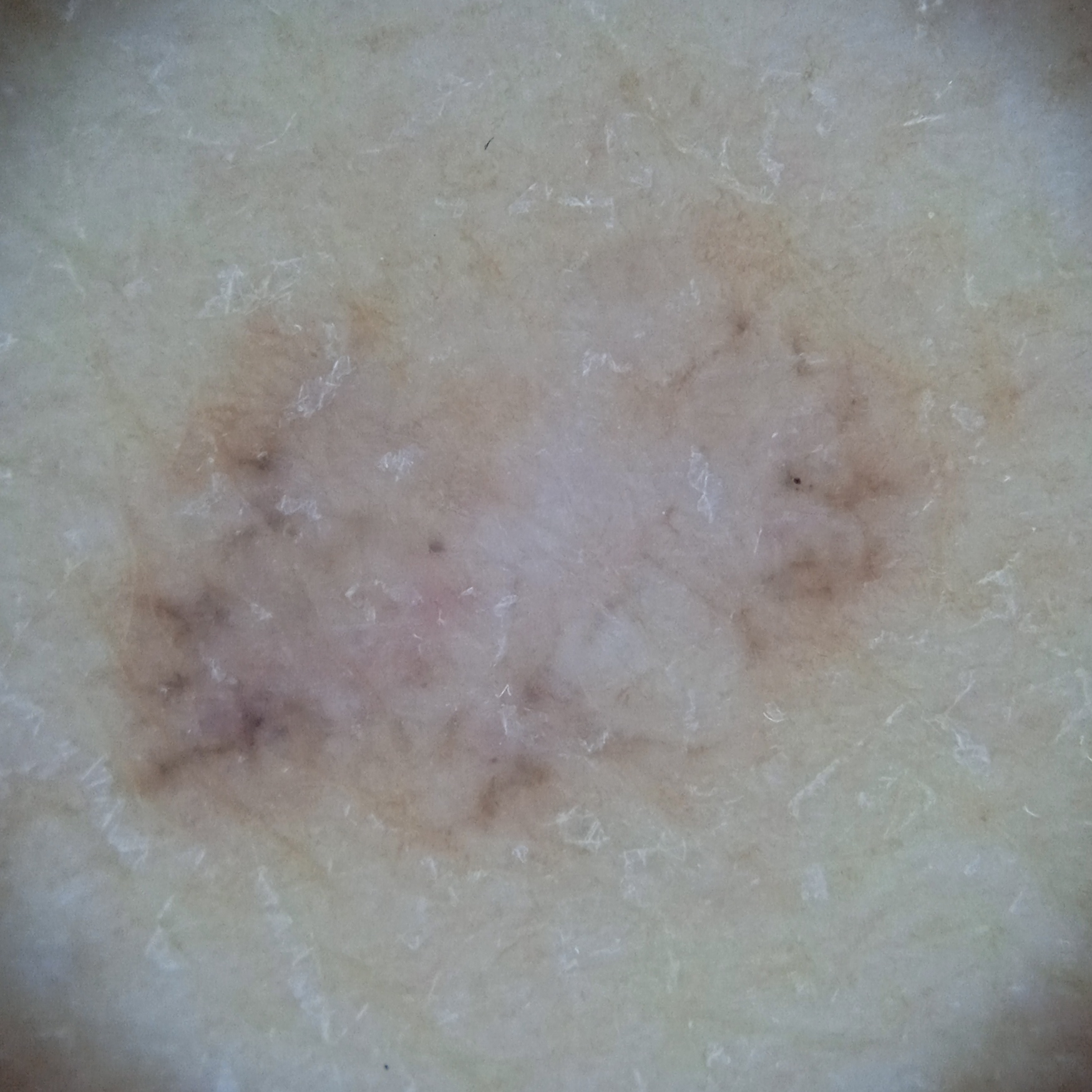image type — dermoscopic image; subject — female, 60 years of age; nevus count — few melanocytic nevi overall; relevant history — a personal history of skin cancer, a personal history of cancer; sun reaction — skin tans without first burning; clinical context — research study (no referral diagnosis); body site — the back; diameter — 10.4 mm; diagnostic label — basal cell carcinoma (dermatologist consensus).